Dermoscopy of a skin lesion:
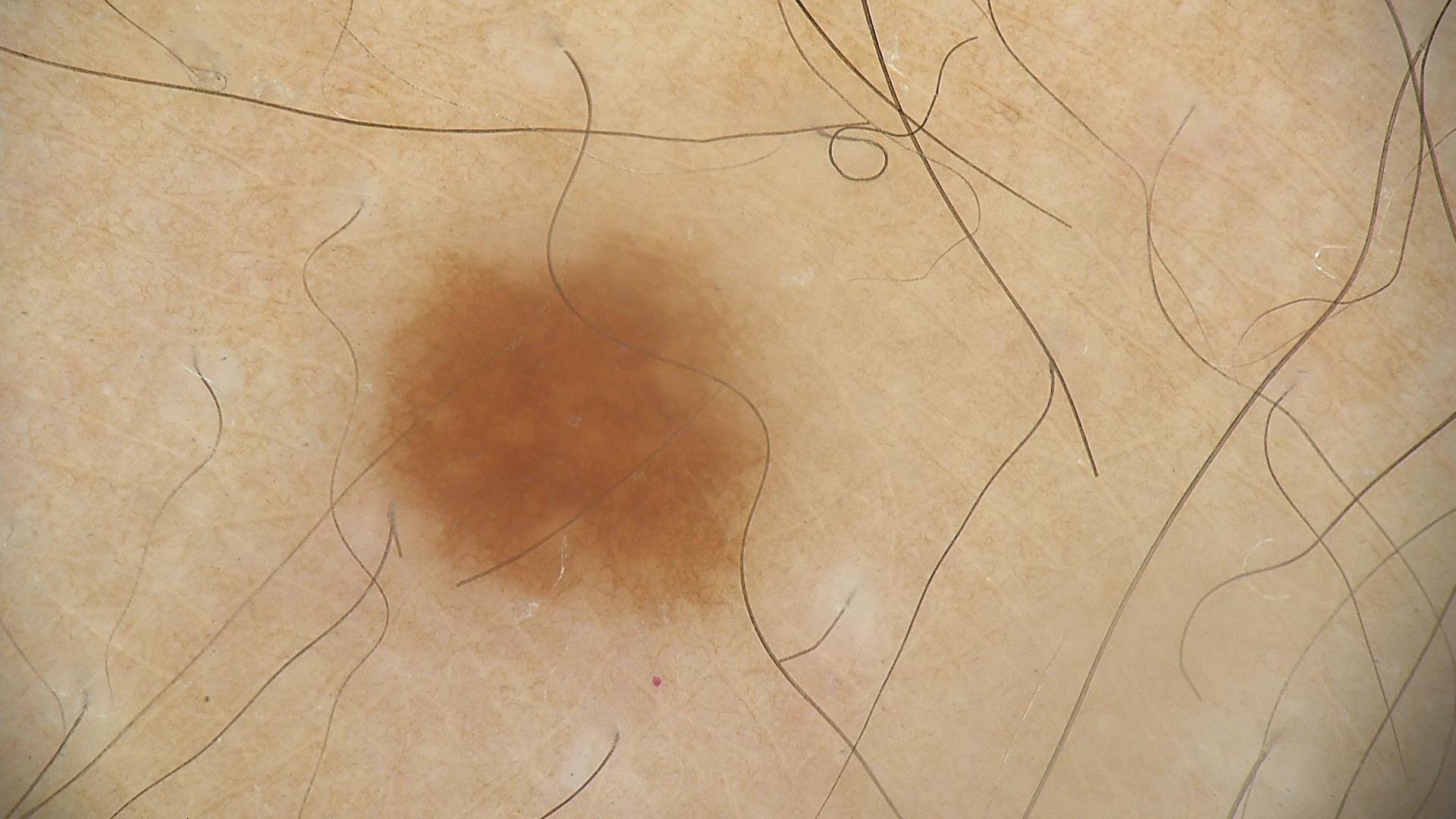Conclusion: Classified as a benign lesion — a dysplastic junctional nevus.